The contributor is a male aged 50–59. Located on the arm. Skin tone: Fitzpatrick phototype IV. Present for less than one week. The lesion is described as flat. No relevant systemic symptoms. An image taken at a distance:
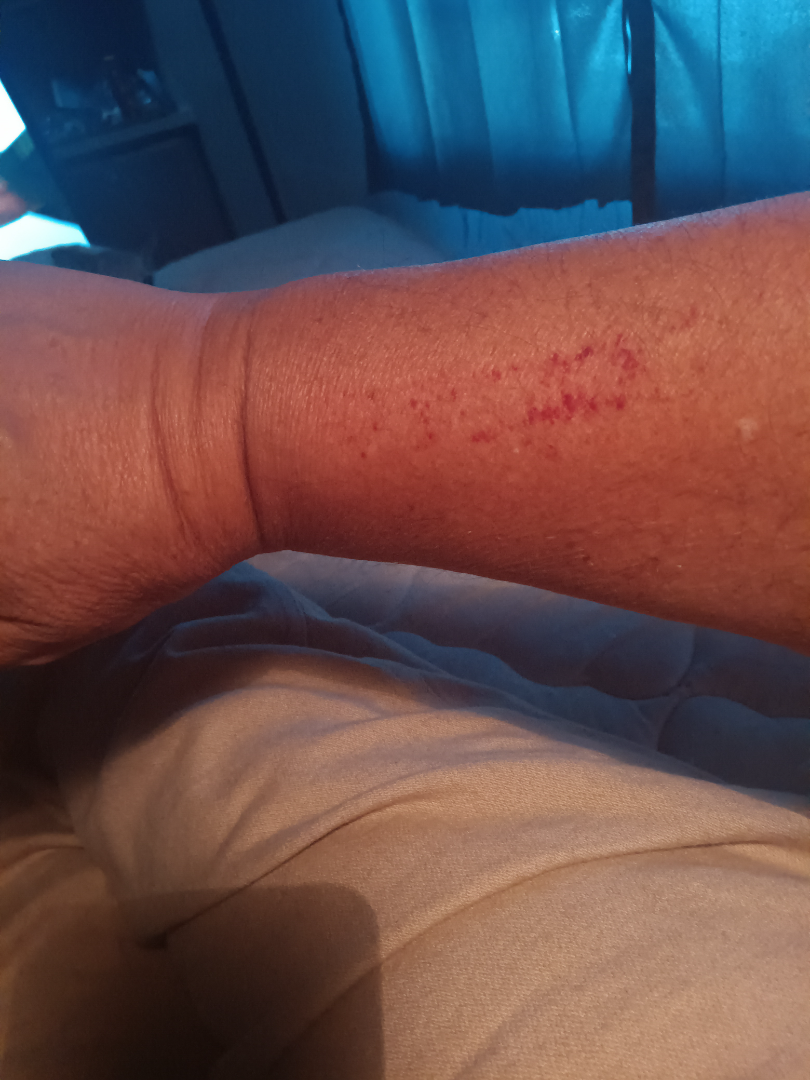  assessment: indeterminate